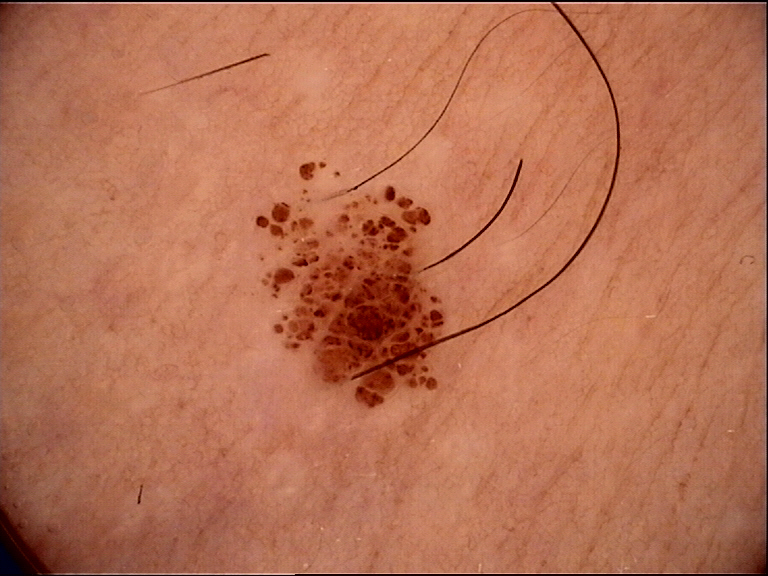Dermoscopy of a skin lesion. Consistent with a banal lesion — a compound nevus.